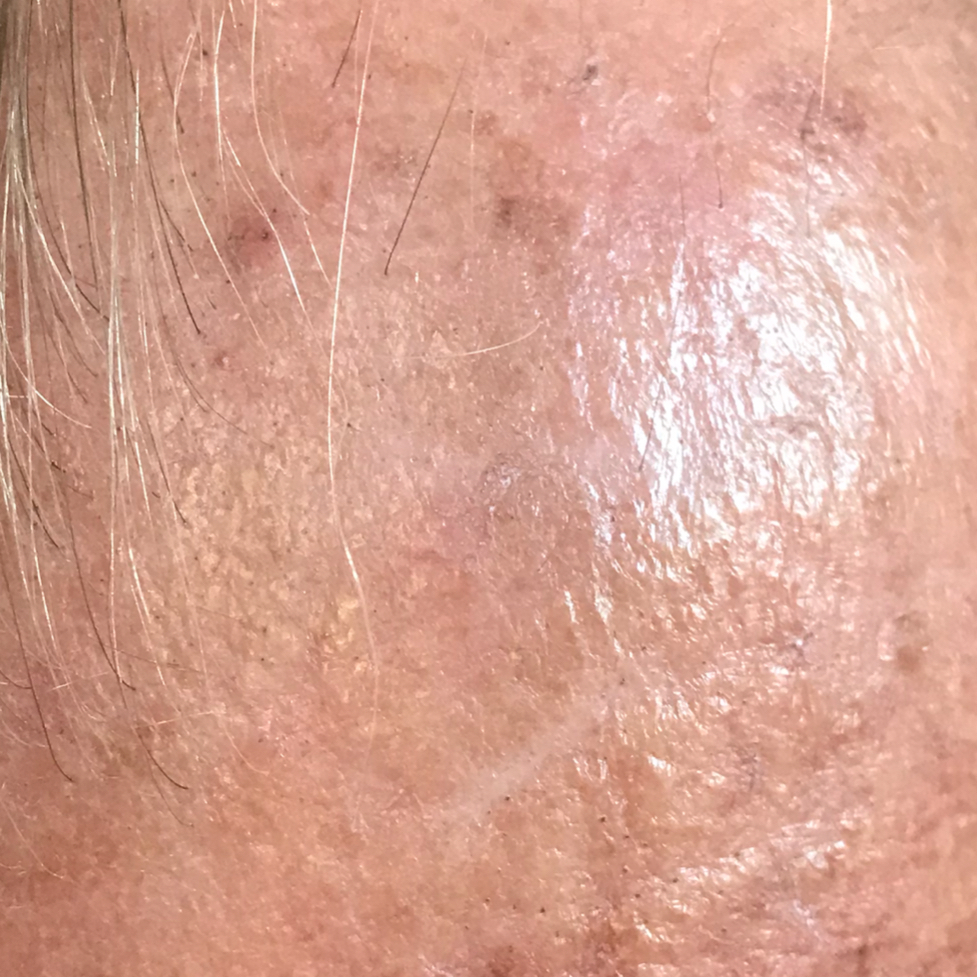Clinical context:
A subject in their late 60s. A smartphone photograph of a skin lesion. The lesion is on the face. Per patient report, the lesion itches.
Conclusion:
The clinical impression was an actinic keratosis.